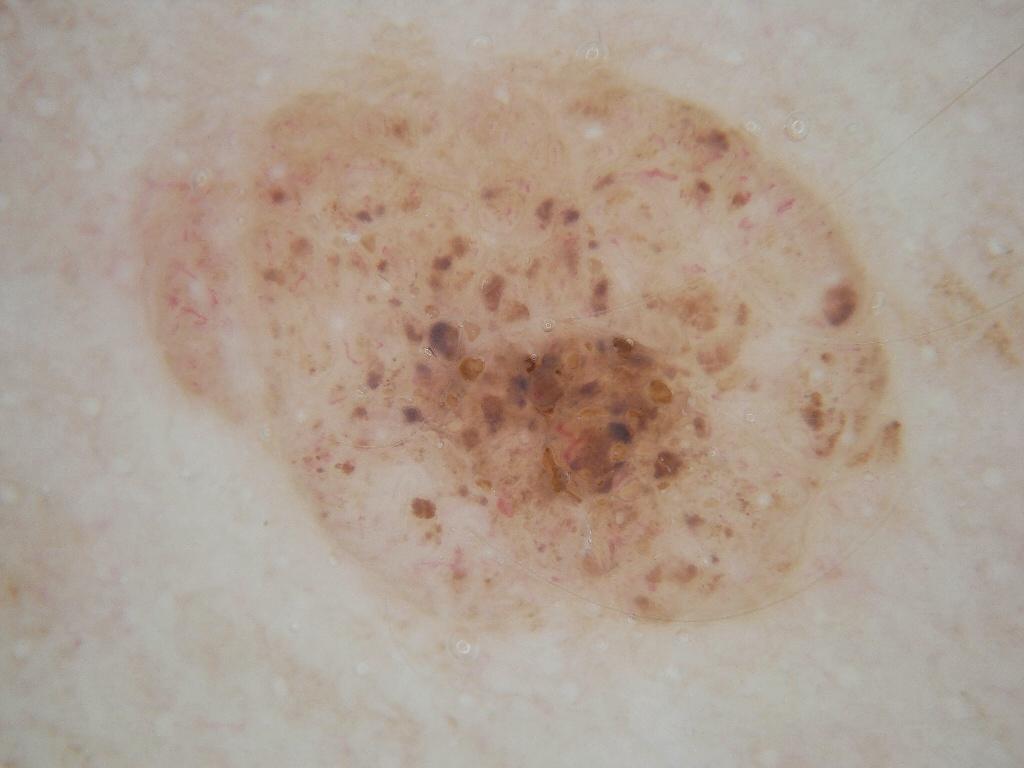Case summary:
* image · dermoscopic image
* lesion size · large
* lesion bbox · [121,43,908,634]
* dermoscopic pattern · globules; absent: streaks, milia-like cysts, pigment network, and negative network
* impression · a melanocytic nevus, a benign lesion